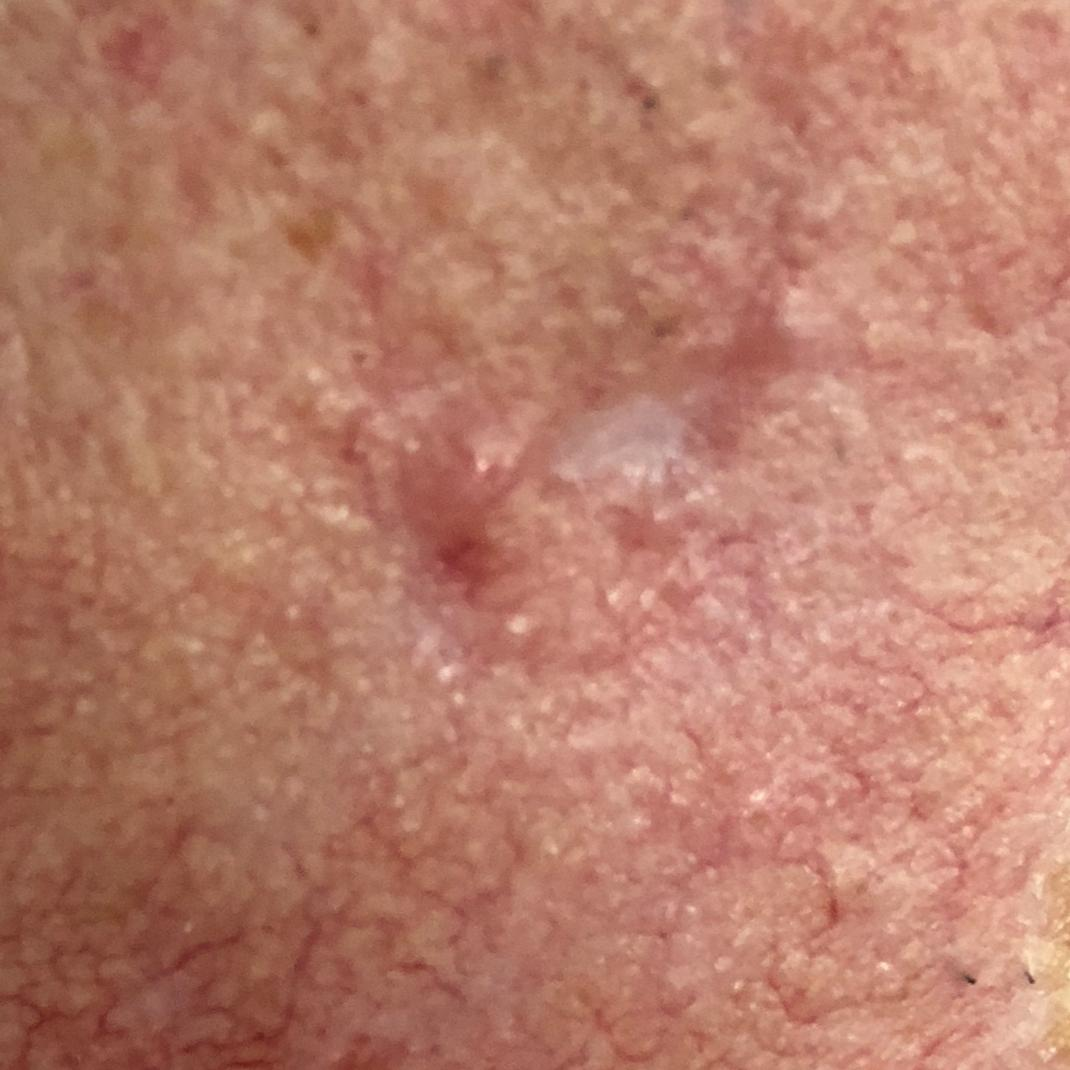A male patient age 78. The lesion is on the face. Per patient report, the lesion itches. Biopsy-confirmed as a basal cell carcinoma.